An image taken at an angle, the leg is involved.
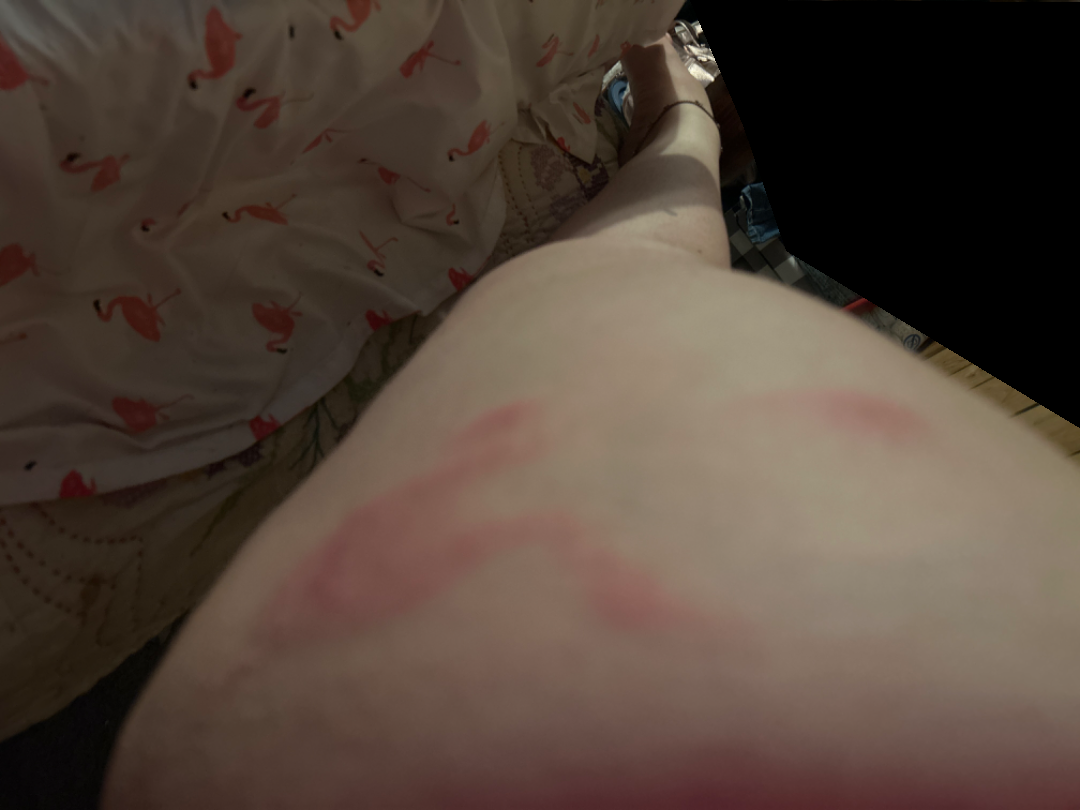<case>
<assessment>not assessable</assessment>
</case>